This is a dermoscopic photograph of a skin lesion, the subject is a female roughly 60 years of age: 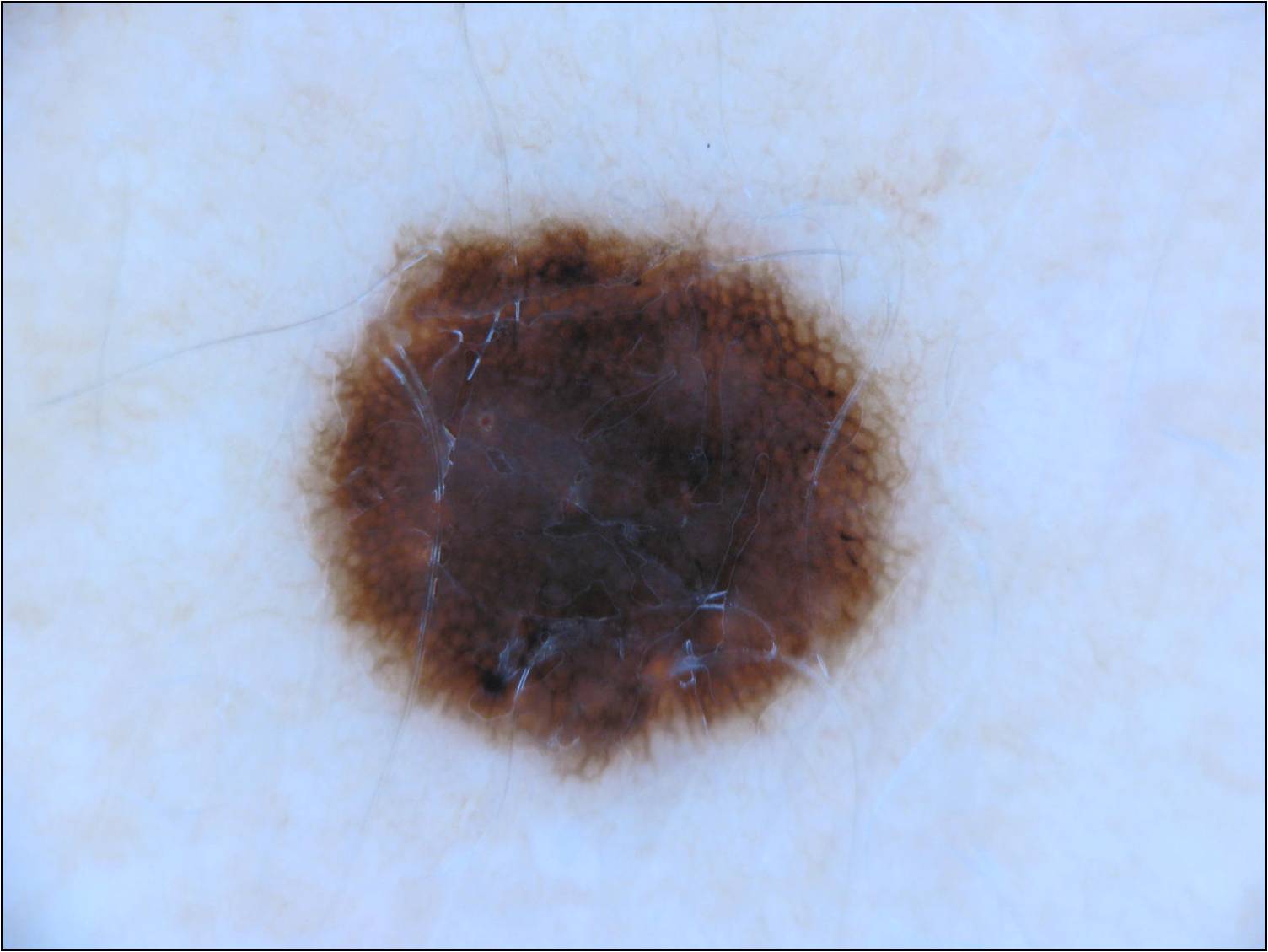Case summary: The lesion is located at 296/206/915/781. On dermoscopy, the lesion shows pigment network, streaks, and globules. The lesion takes up about 22% of the image. Impression: The diagnostic assessment was a melanocytic nevus, a benign lesion.